This is a close-up image — 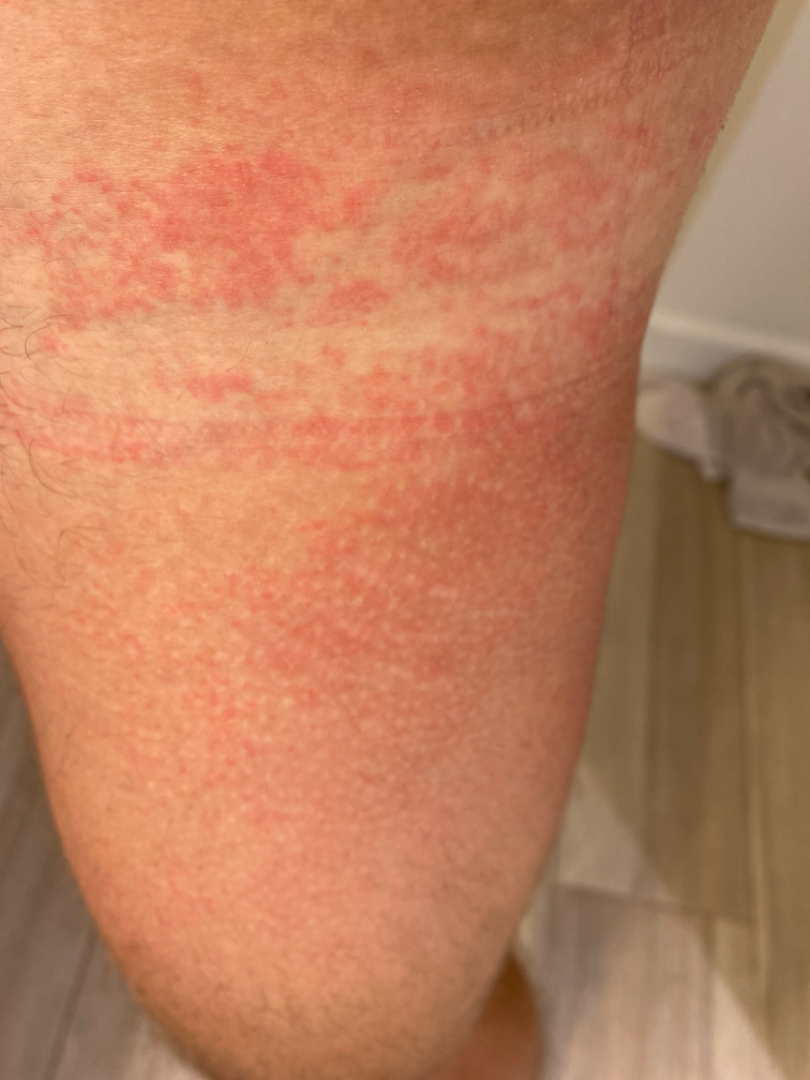Background:
The lesion is associated with itching. FST III. The patient described the issue as a rash.
Findings:
On dermatologist assessment of the image, Acute dermatitis, NOS; Allergic Contact Dermatitis; and Irritant Contact Dermatitis were considered with similar weight.